A female patient in their late 70s. A clinical photo of a skin lesion taken with a smartphone:
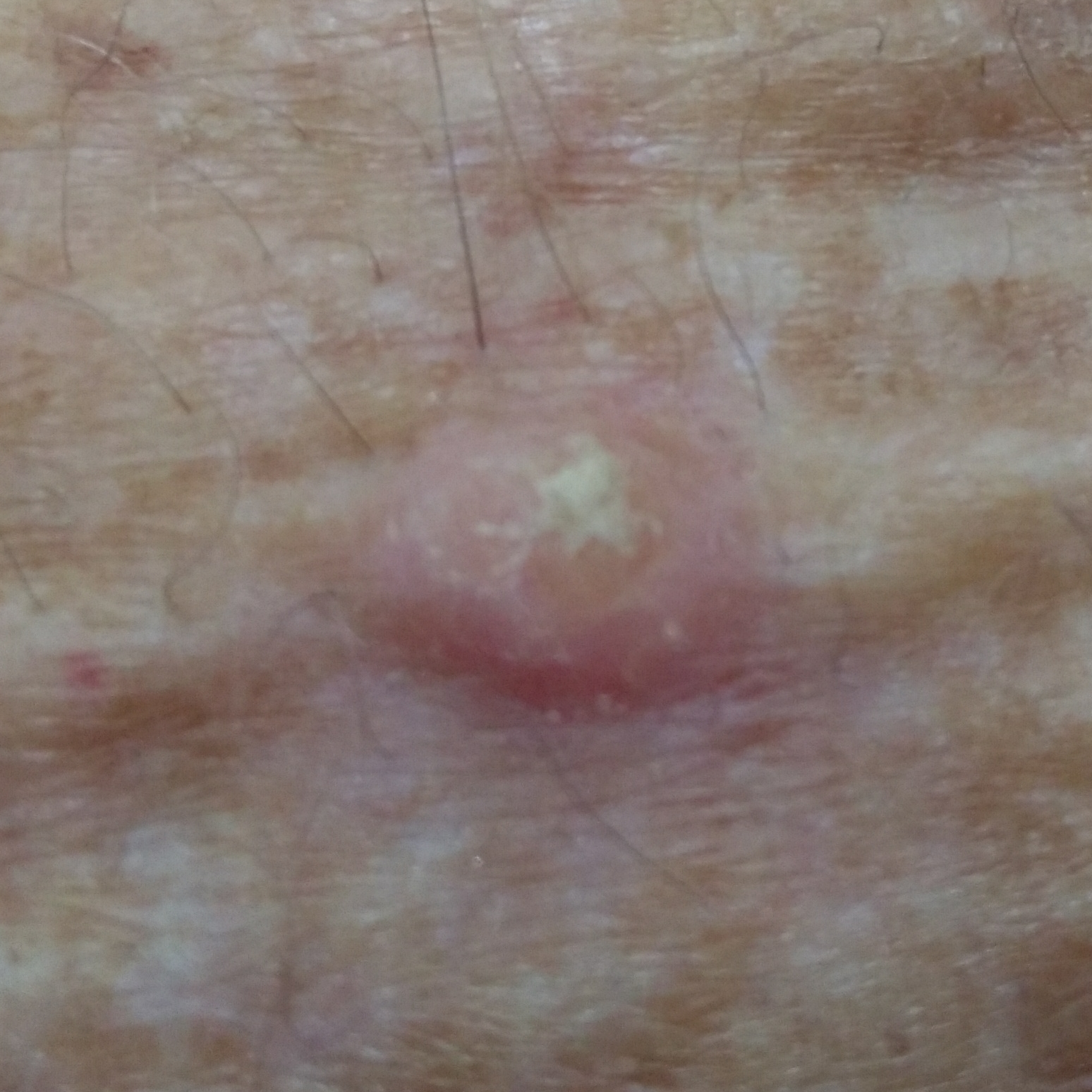Patient and lesion:
The lesion involves a forearm. Per patient report, the lesion itches and is elevated.
Pathology:
On biopsy, the diagnosis was an actinic keratosis.